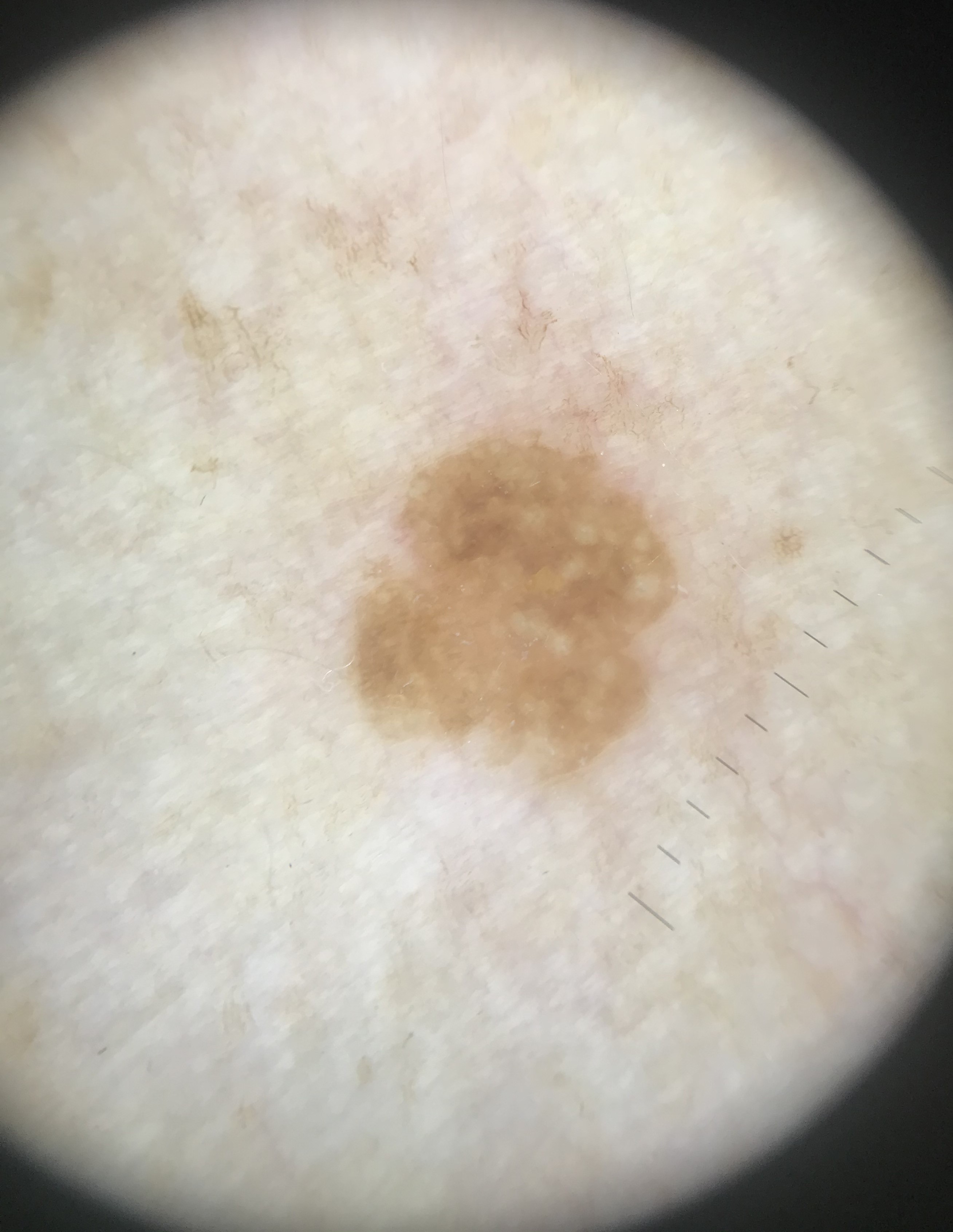image: dermatoscopy
diagnosis:
  name: seborrheic keratosis
  code: sk
  malignancy: benign
  super_class: non-melanocytic
  confirmation: expert consensus